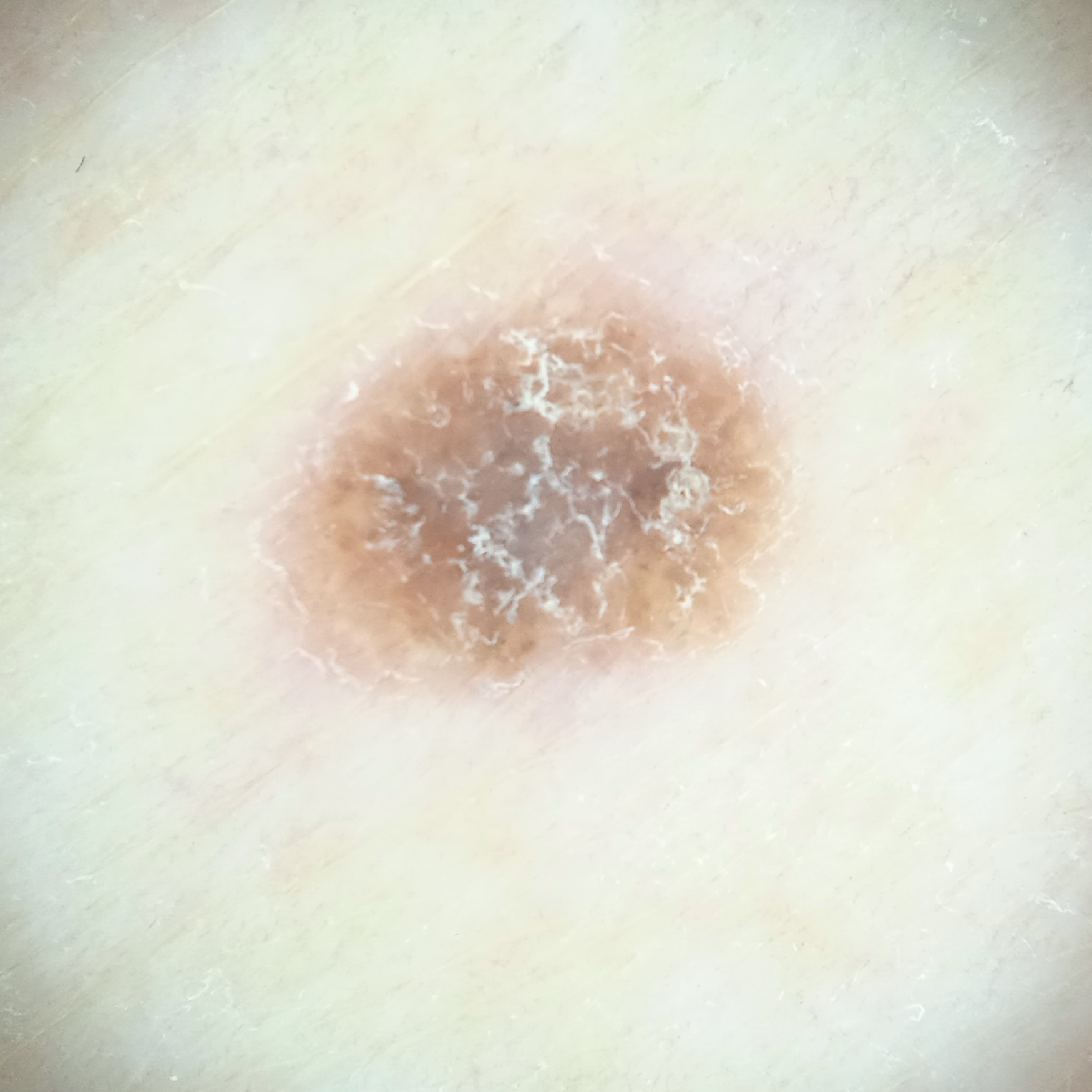The patient says their skin tans without first burning. The patient describes having few moles overall. A male subject age 79. Measuring roughly 5.9 mm. The dermatologists' assessment was a seborrheic keratosis.